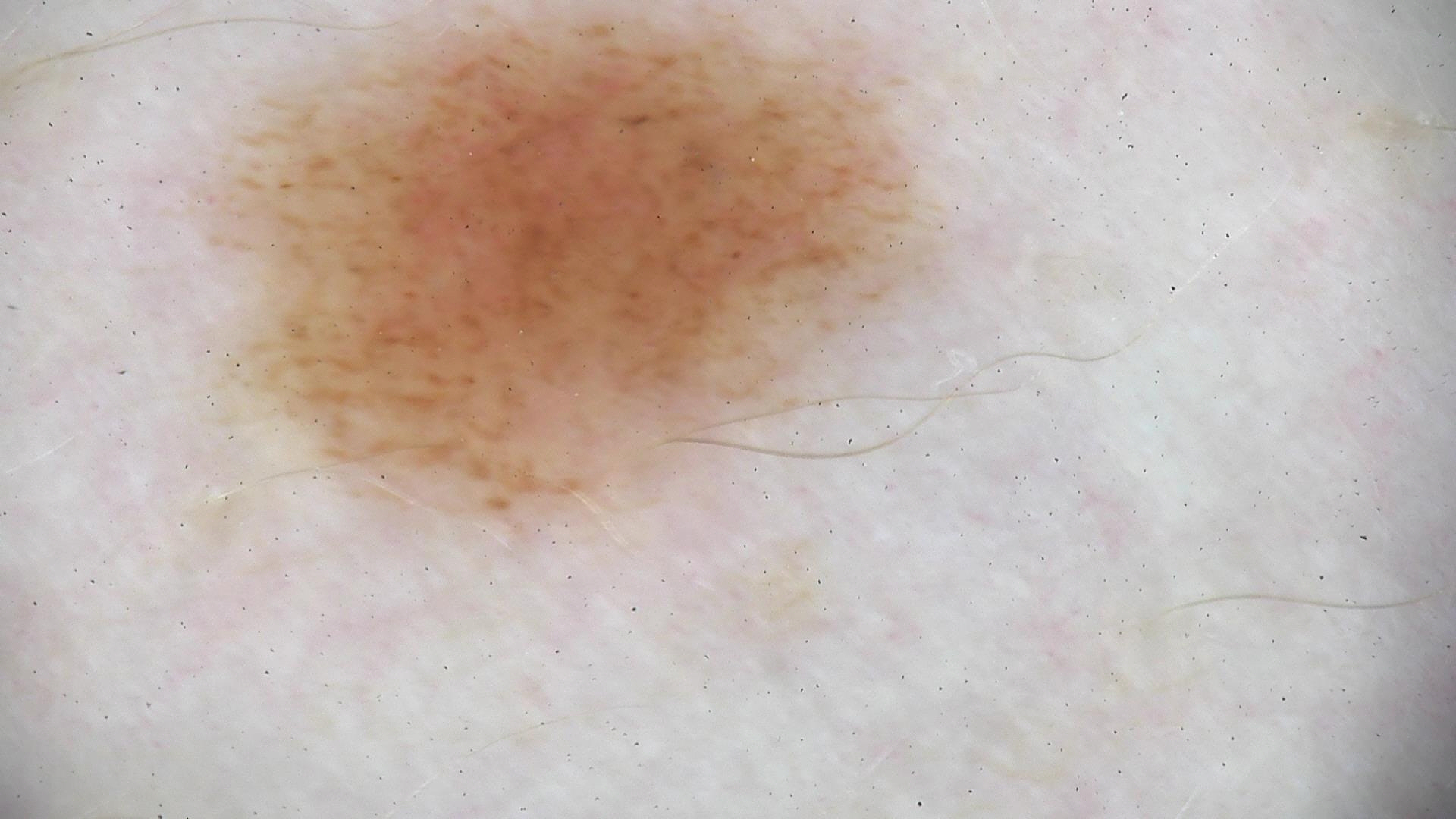label = dysplastic junctional nevus (expert consensus).